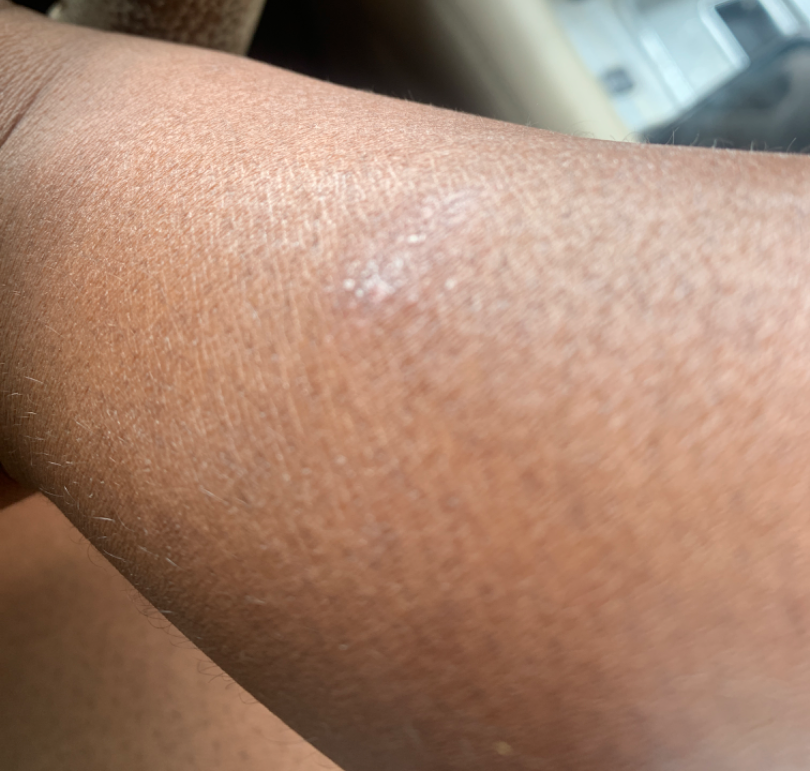The contributor is 30–39, female. Close-up view. Fitzpatrick skin type V. The arm is involved. The lesion is described as flat. Self-categorized by the patient as a rash. The patient reports itching. Psoriasis (considered); Eczema (considered).